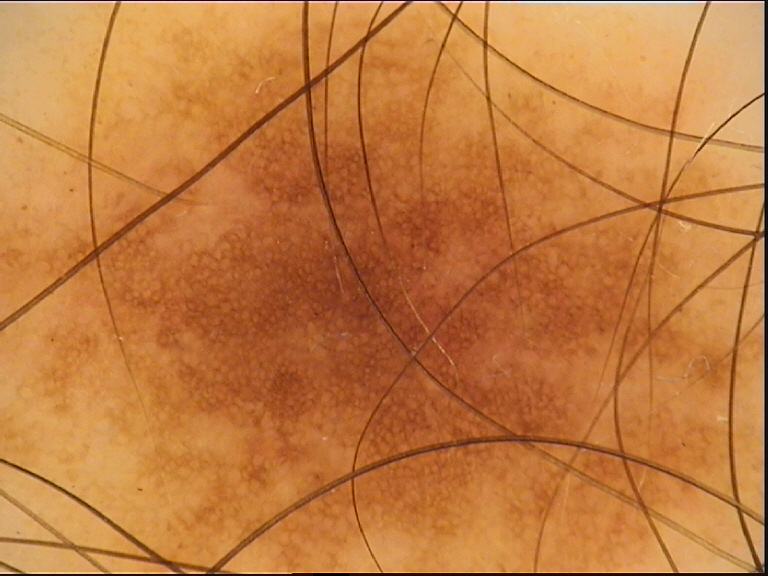Diagnosed as a banal lesion — a junctional nevus.